This is a dermoscopic photograph of a skin lesion:
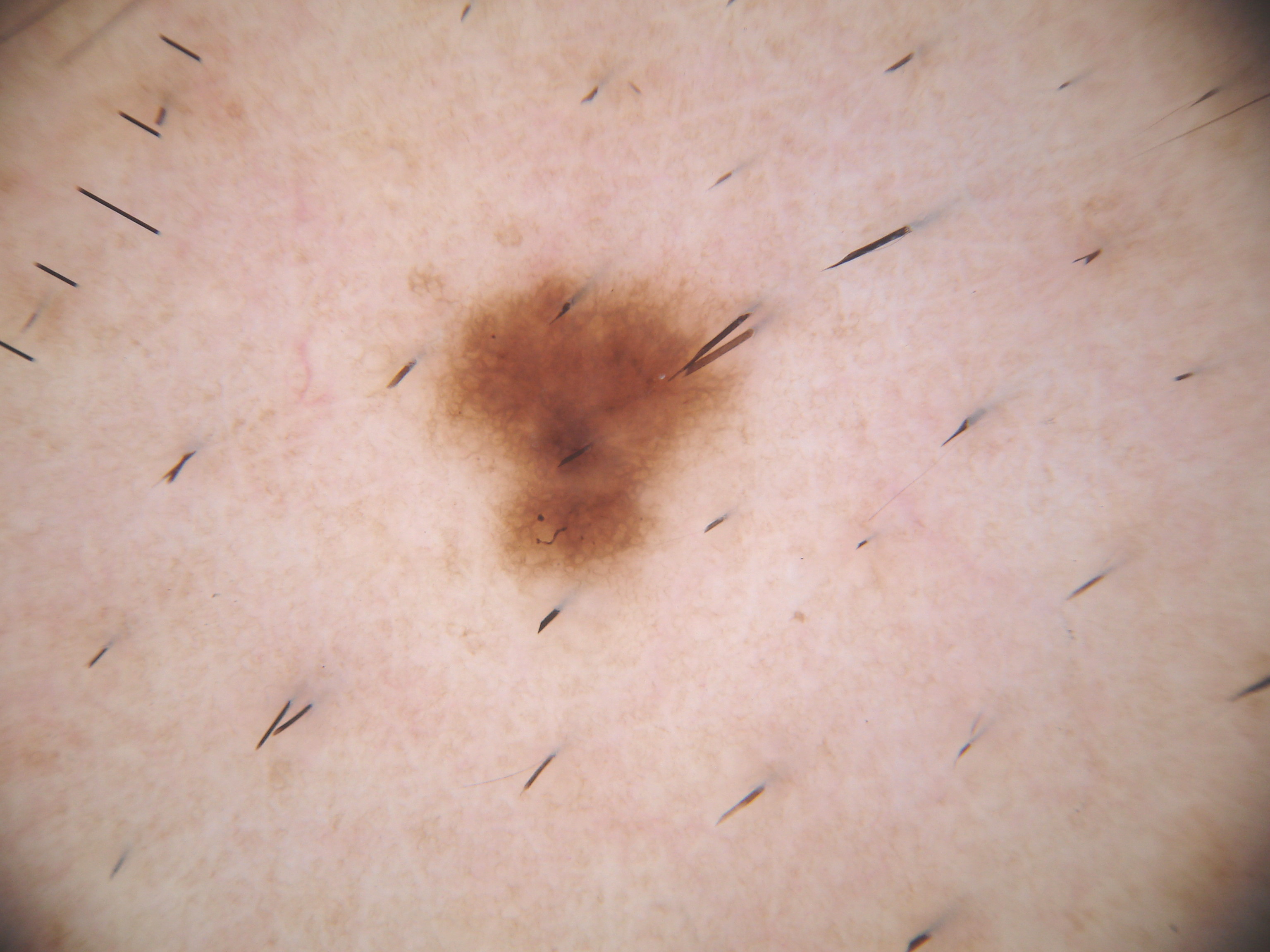features: pigment network; bounding box: left=397, top=257, right=768, bottom=596; diagnosis: a melanocytic nevus.